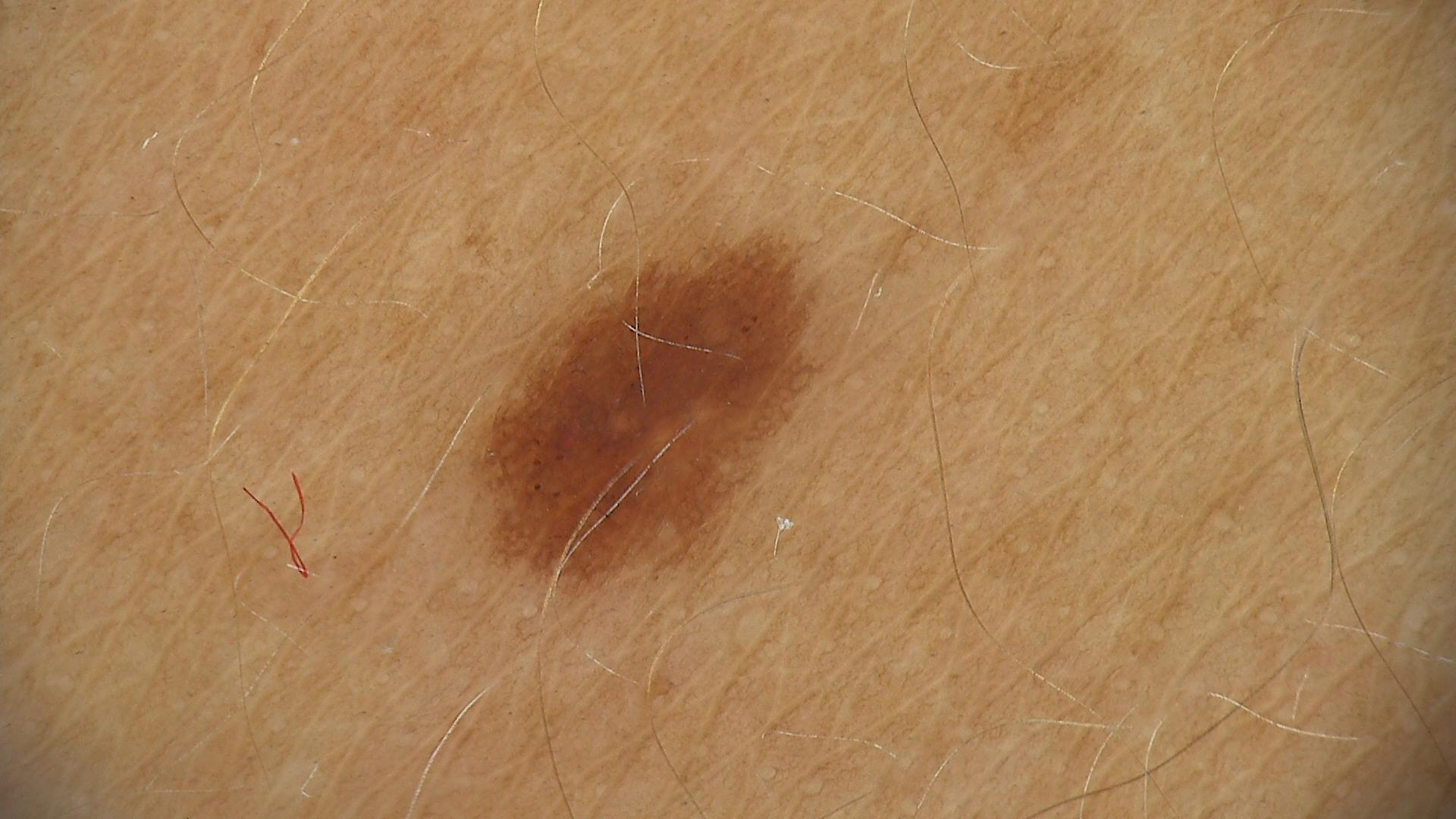| key | value |
|---|---|
| diagnostic label | dysplastic junctional nevus (expert consensus) |